A skin lesion imaged with a dermatoscope: 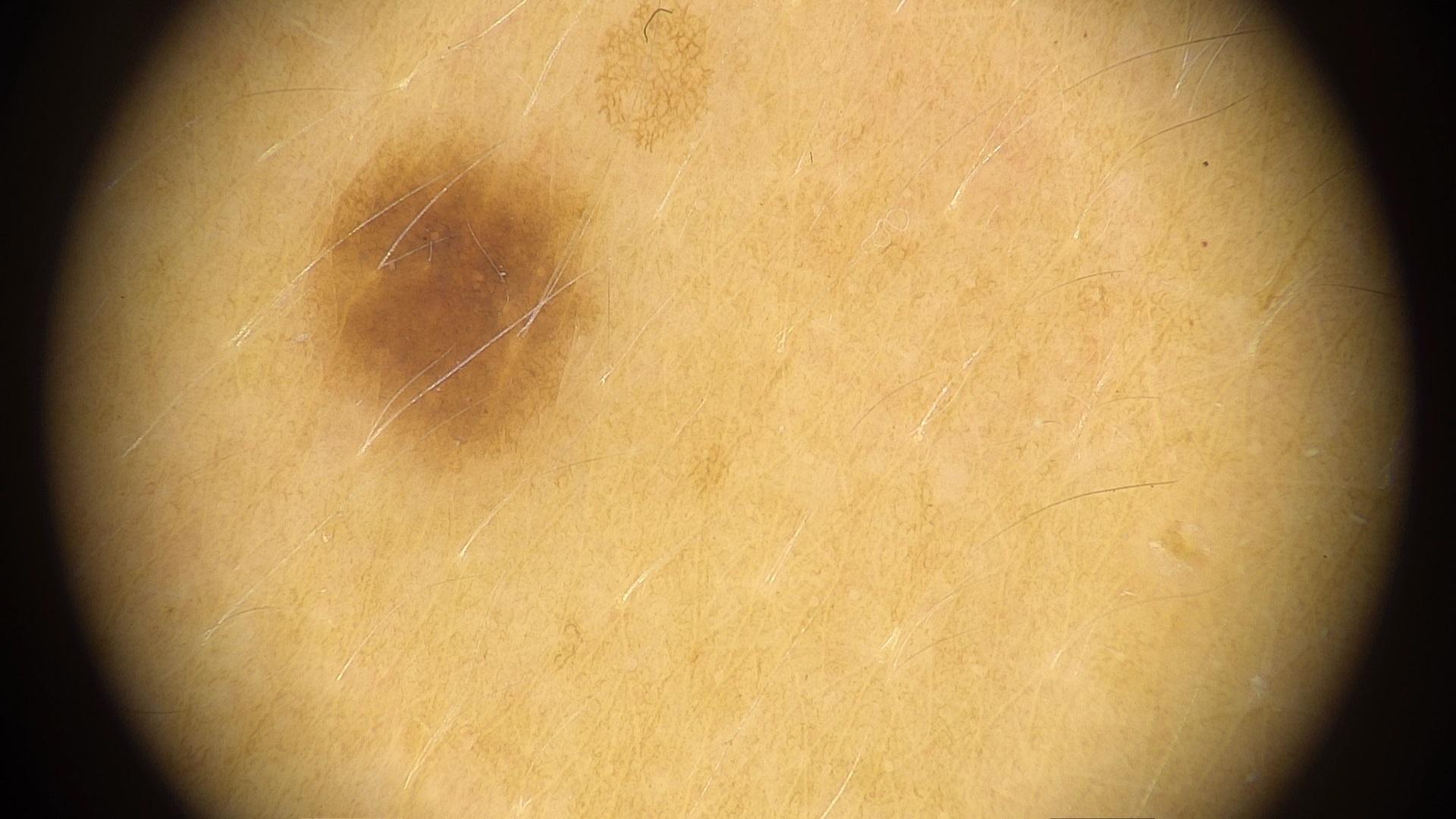{"lesion_location": {"region": "the trunk", "detail": "the posterior trunk"}, "diagnosis": {"name": "Nevus", "malignancy": "benign", "confirmation": "expert clinical impression", "lineage": "melanocytic"}}